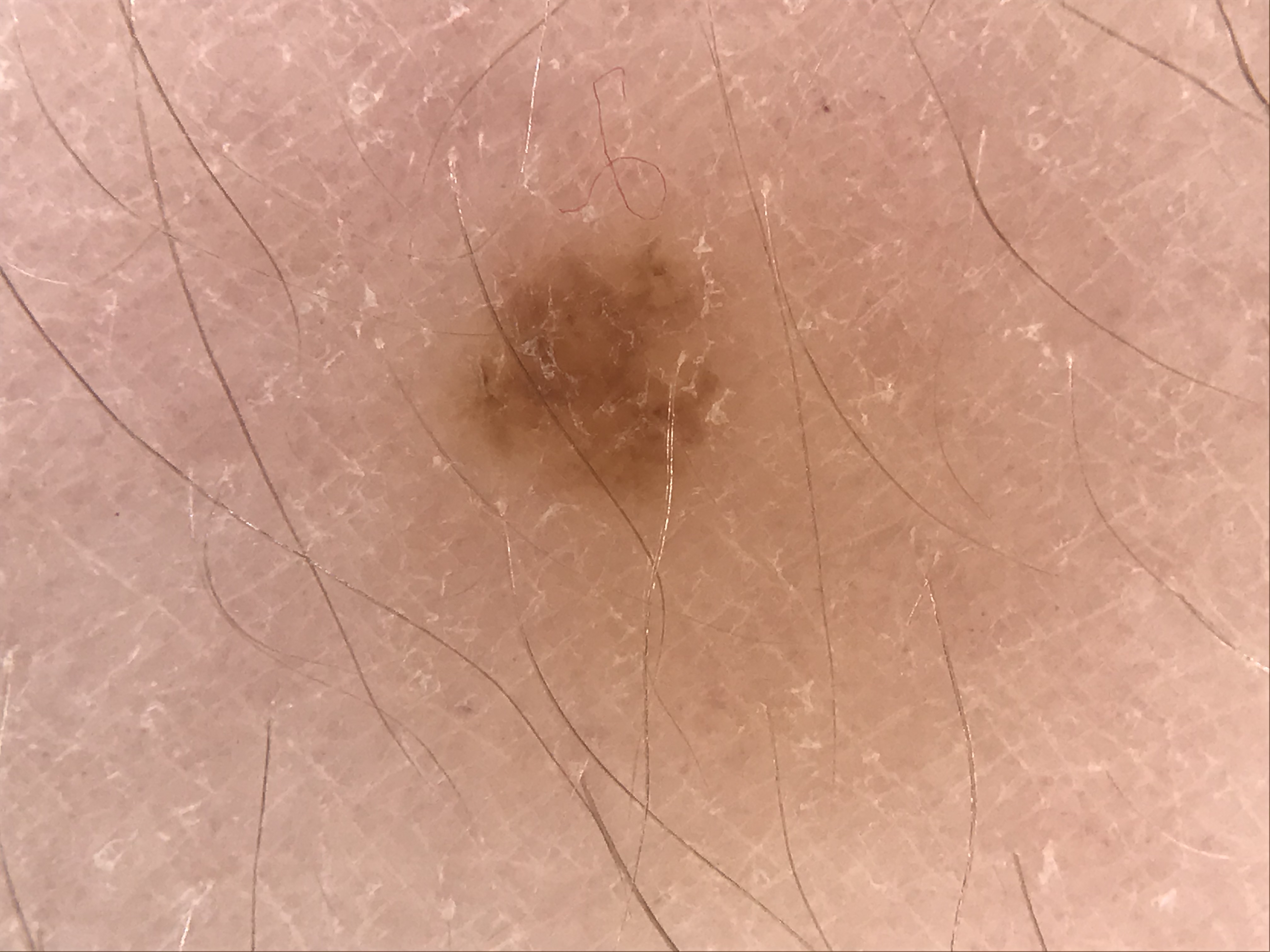{
  "diagnosis": {
    "name": "dysplastic junctional nevus",
    "code": "jd",
    "malignancy": "benign",
    "super_class": "melanocytic",
    "confirmation": "expert consensus"
  }
}